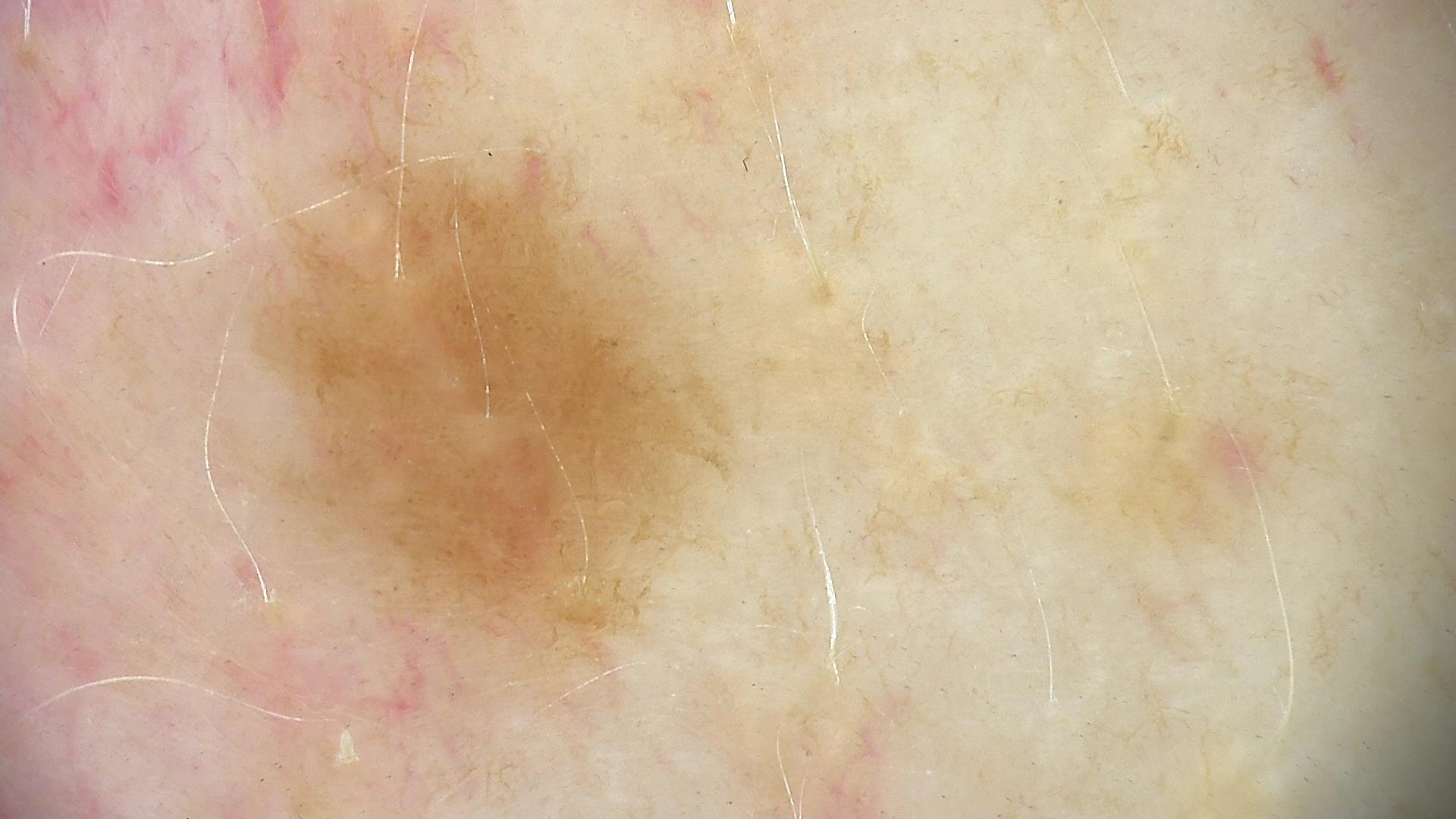Consistent with a benign lesion — a dysplastic junctional nevus.